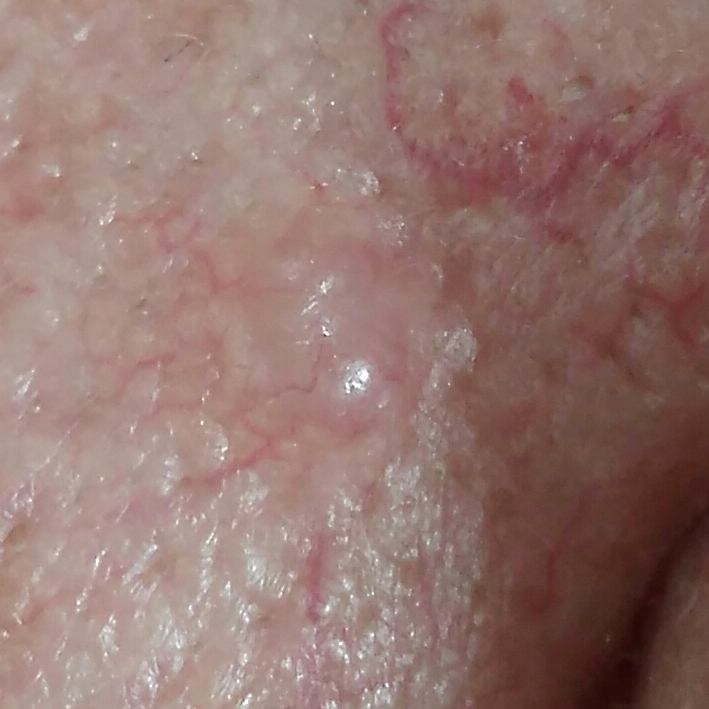Patient and lesion: A clinical photograph showing a skin lesion. A male patient 70 years old. The lesion involves the nose. The patient describes that the lesion itches, is elevated, and has grown. Diagnosis: Biopsy-confirmed as a basal cell carcinoma.